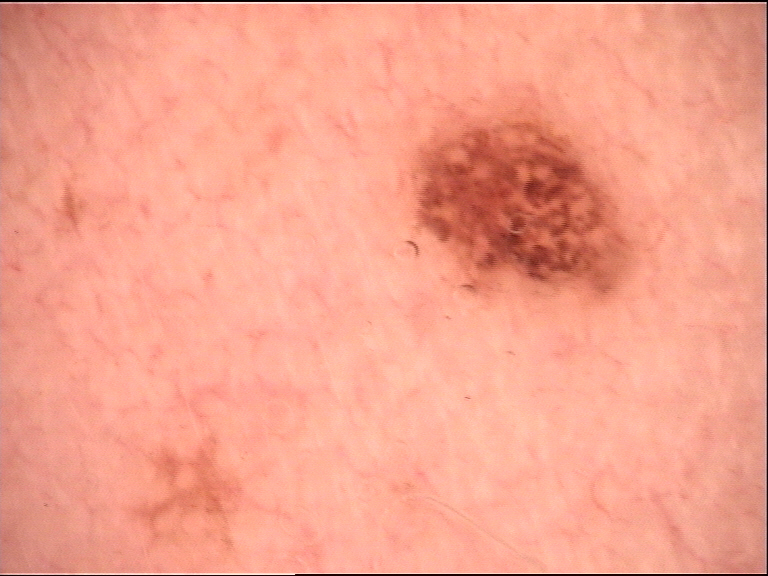Summary: A dermoscopy image of a single skin lesion. The morphology is that of a banal lesion. Conclusion: The diagnosis was a compound nevus.